A dermoscopic photograph of a skin lesion.
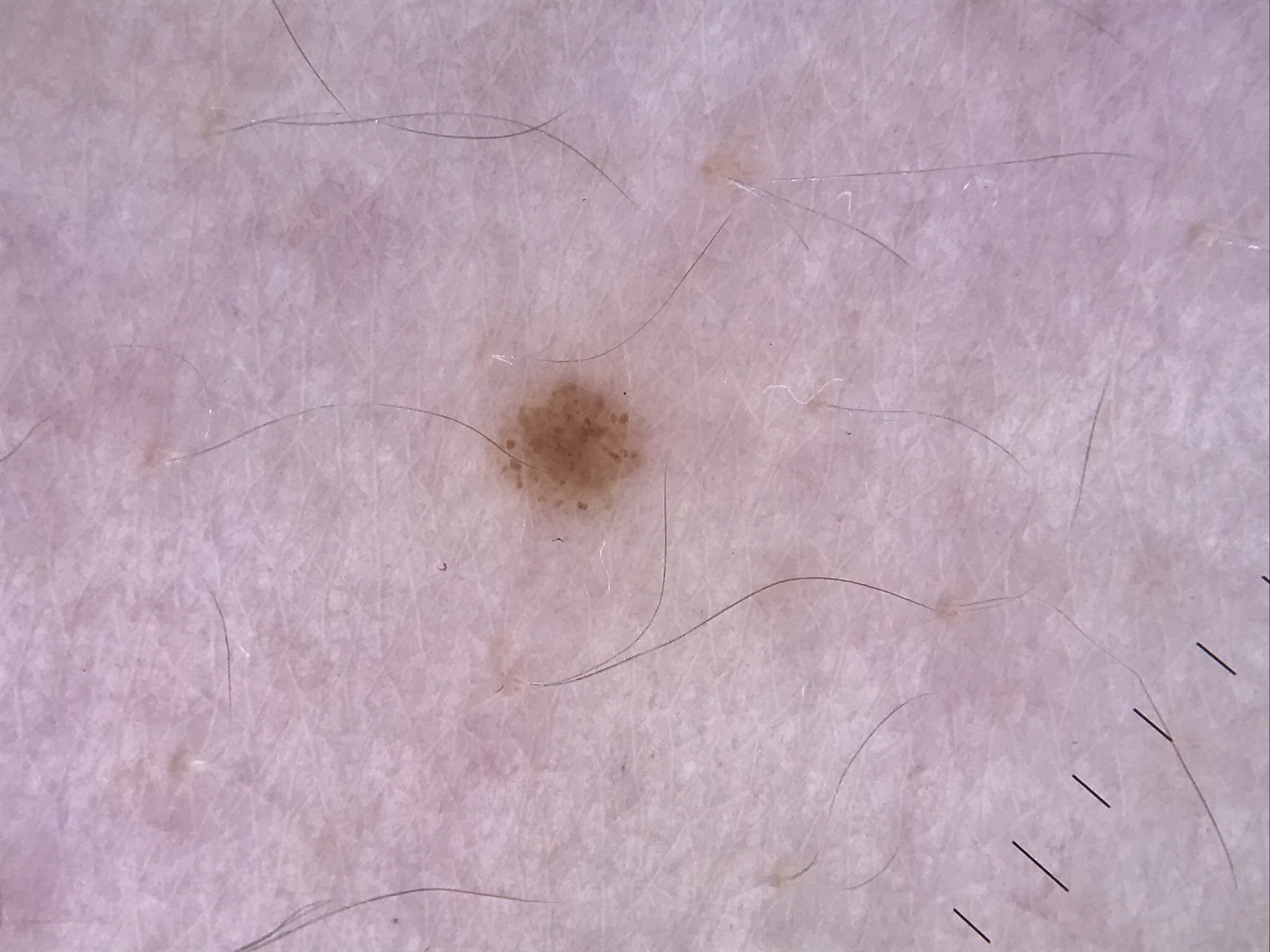| feature | finding |
|---|---|
| diagnostic label | dysplastic junctional nevus (expert consensus) |